The patient indicates the condition has been present for three to twelve months · the contributor is male · the patient described the issue as a rash · the affected area is the leg · the photo was captured at a distance · the lesion is associated with bothersome appearance and itching · the patient indicates the lesion is raised or bumpy — 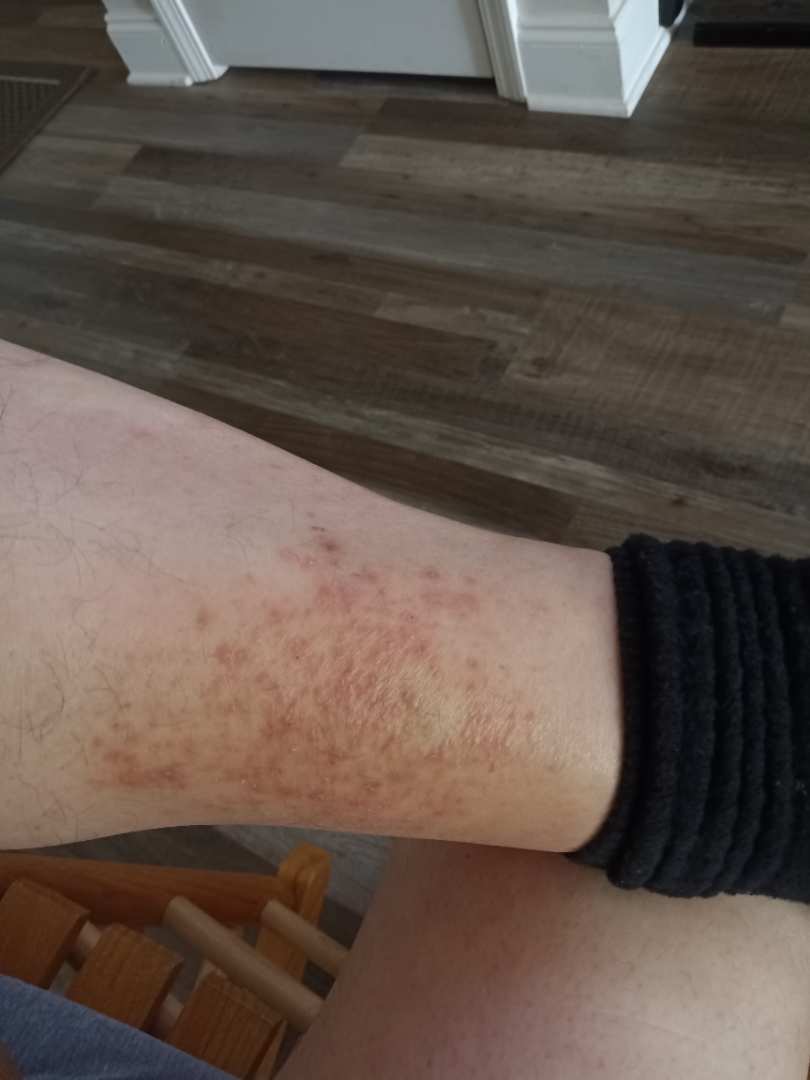On photographic review, Eczema (0.43); Acute and chronic dermatitis (0.21); Allergic Contact Dermatitis (0.18); Pigmented purpuric eruption (0.09); Drug Rash (0.09).